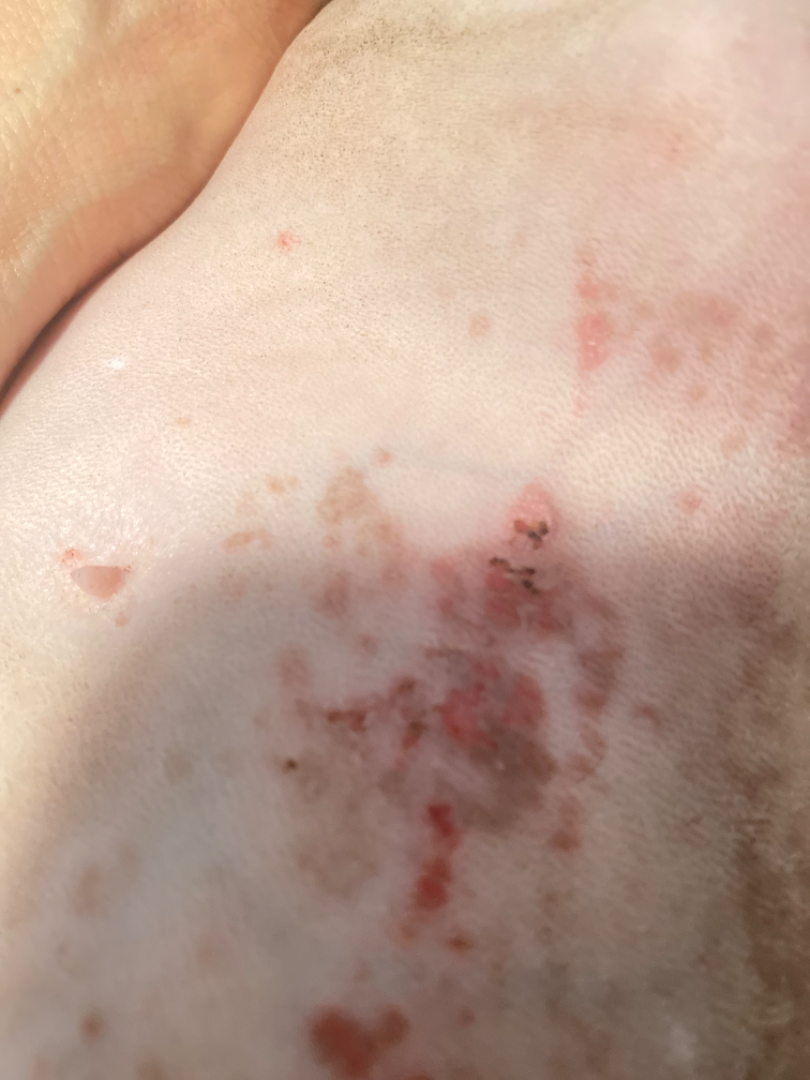assessment=could not be assessed | shot type=at an angle.